Located on the back of the torso, arm, leg and front of the torso. The patient considered this a rash. The lesion is described as raised or bumpy and rough or flaky. Female contributor, age 50–59. This image was taken at a distance. Associated systemic symptoms include chills. Reported lesion symptoms include burning, pain, bothersome appearance and itching. Skin tone: Fitzpatrick skin type II; non-clinician graders estimated Monk skin tone scale 2 or 4. Present for one to three months: 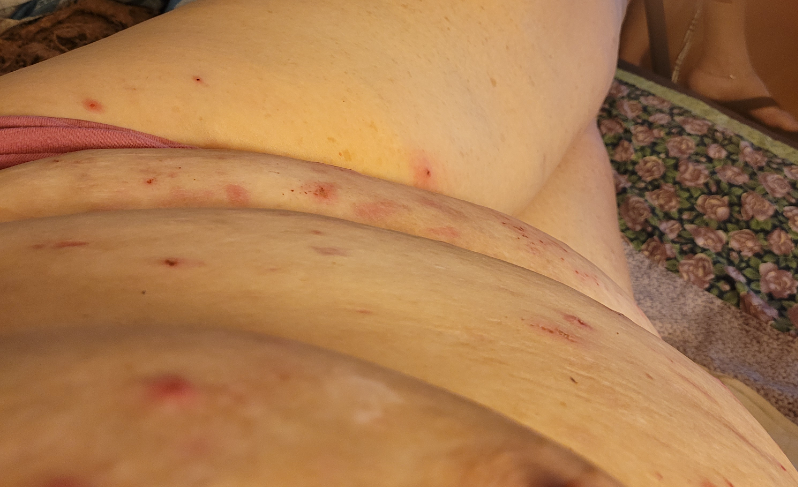assessment — three independent reviewers: the leading consideration is Prurigo nodularis; possibly Lichen Simplex Chronicus; the differential also includes Pemphigus foliaceus; also consider Eczema